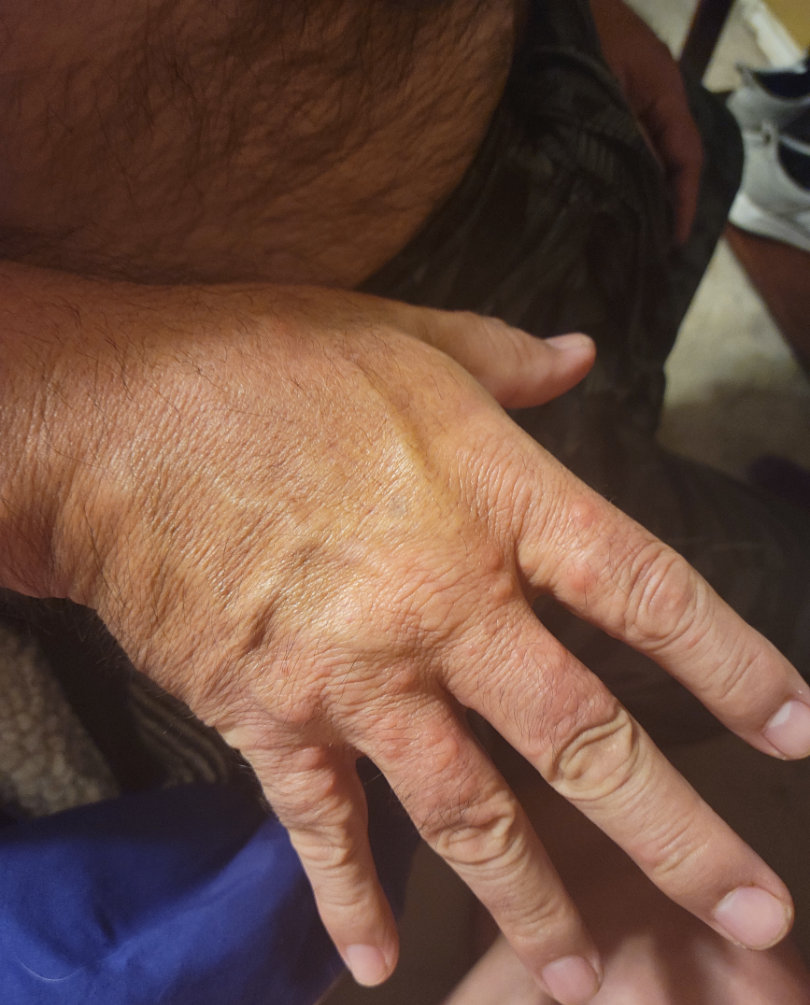The contributor is male.
An image taken at a distance.
The affected area is the back of the hand.
On remote dermatologist review: Histiocytosis of skin (40%); Insect Bite (40%); Lichenoid myxedema (20%).